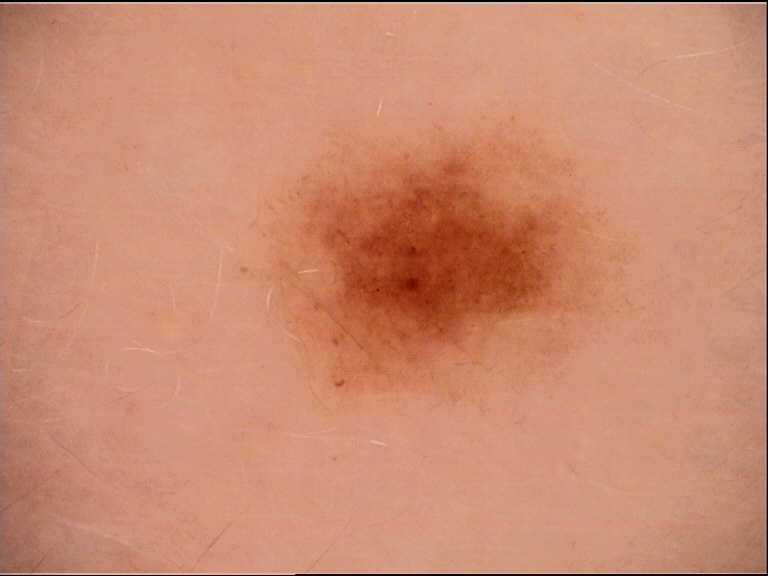Q: What is the diagnosis?
A: junctional nevus (expert consensus)